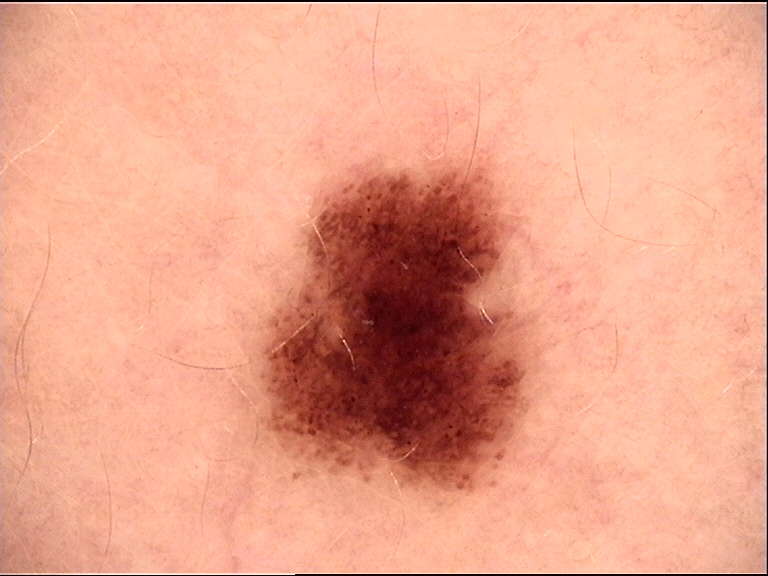The diagnosis was a dysplastic junctional nevus.